Reported duration is one to three months · the affected area is the palm · this image was taken at a distance · texture is reported as raised or bumpy · the patient reports enlargement — 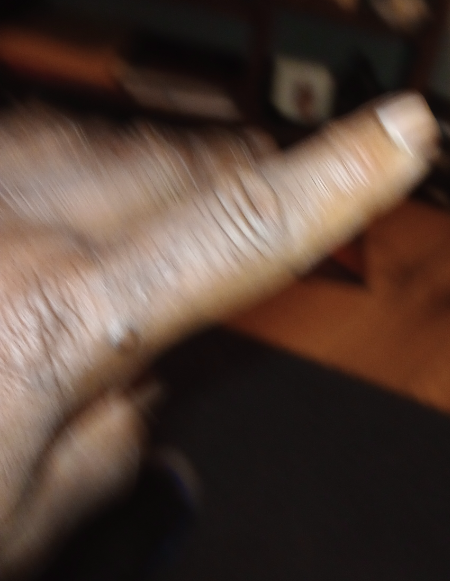On remote dermatologist review, most likely Cyst; also consider Dermatofibroma; less likely is Calcinosis cutis.